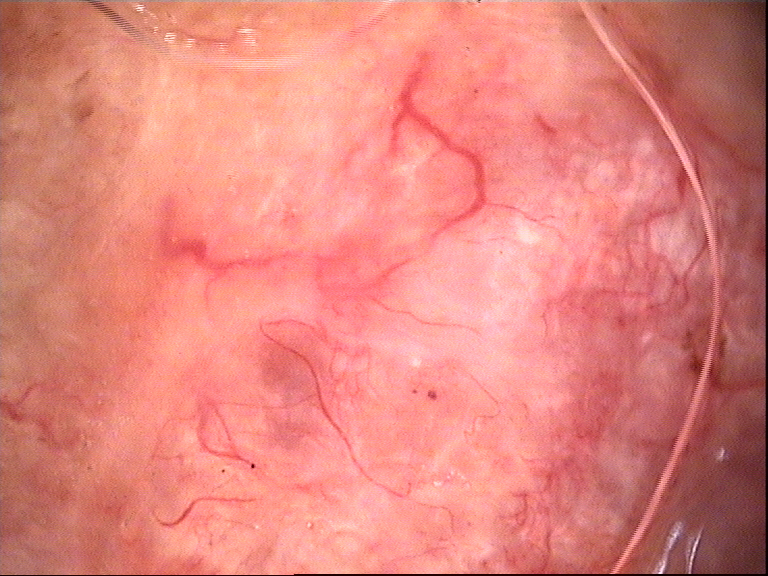Q: What kind of image is this?
A: dermatoscopy
Q: What kind of lesion is this?
A: keratinocytic
Q: What did the workup show?
A: basal cell carcinoma (biopsy-proven)